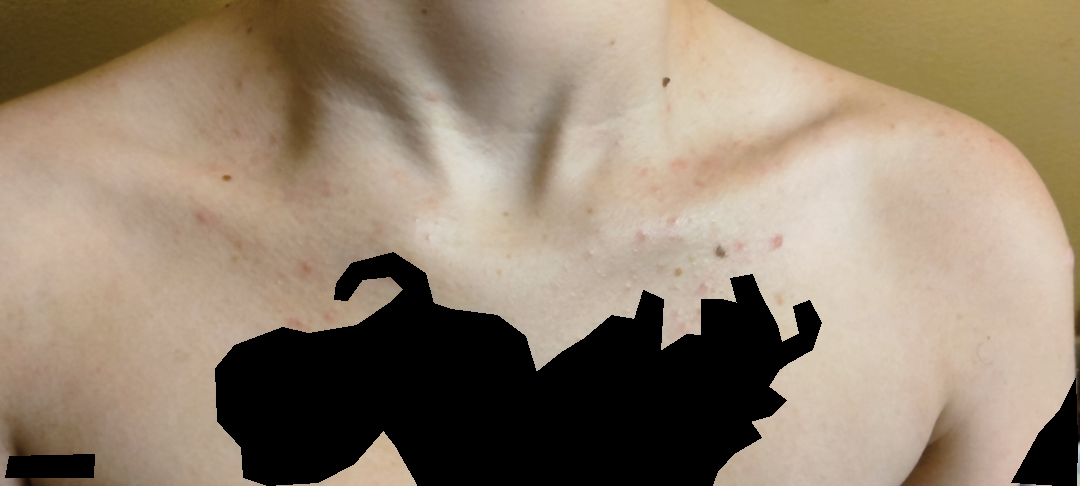location=head or neck, front of the torso and back of the torso | subject=female, age 18–29 | reported symptoms=bothersome appearance and enlargement | patient's own categorization=a rash | surface texture=raised or bumpy | shot type=at a distance | symptom duration=less than one week | differential=Acne (most likely); Folliculitis (considered); Allergic Contact Dermatitis (remote).